A dermatoscopic image of a skin lesion: 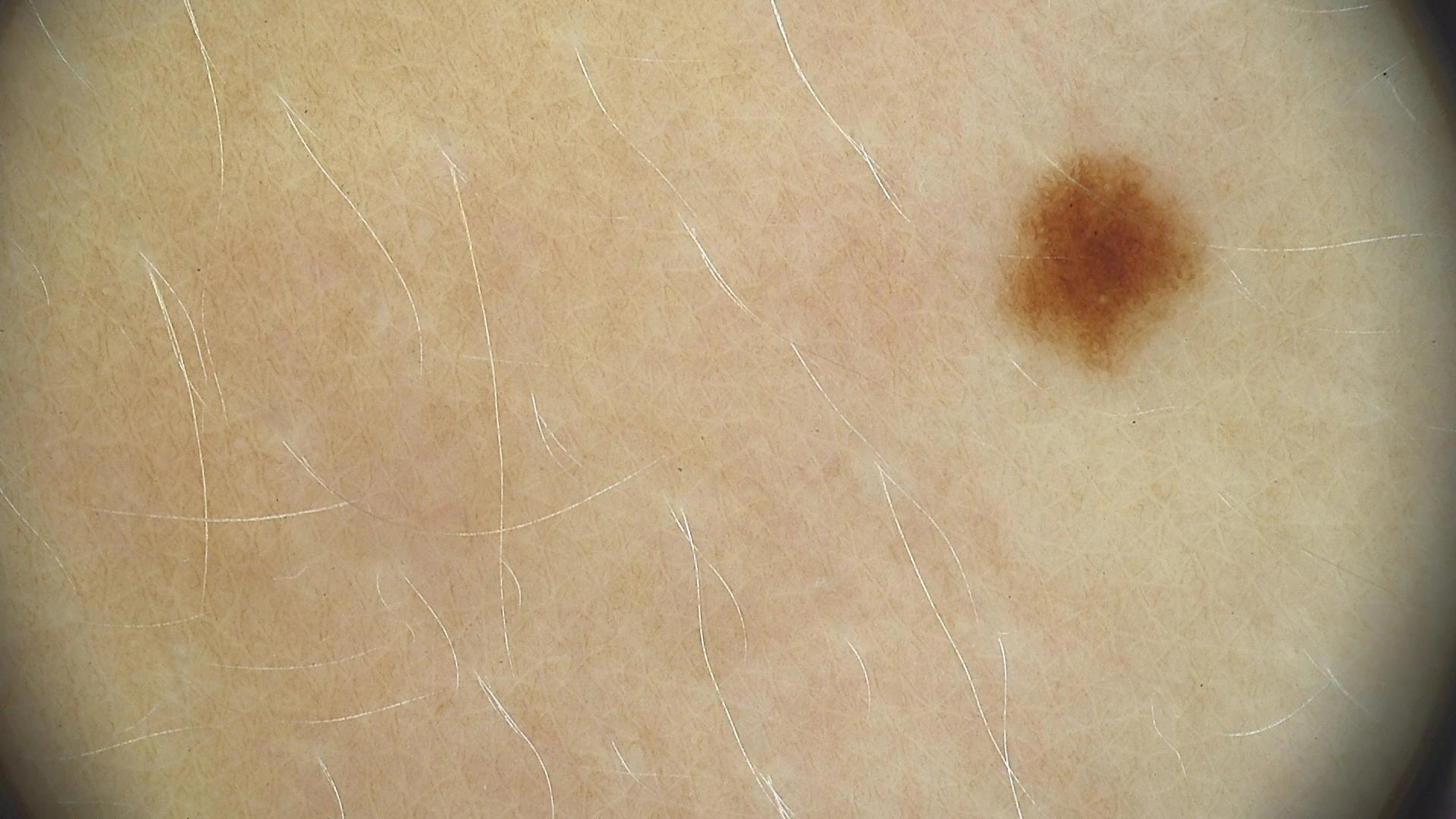Classified as a banal lesion — a junctional nevus.